This image was taken at a distance · the lesion involves the back of the hand and arm · the patient is a female aged 30–39: 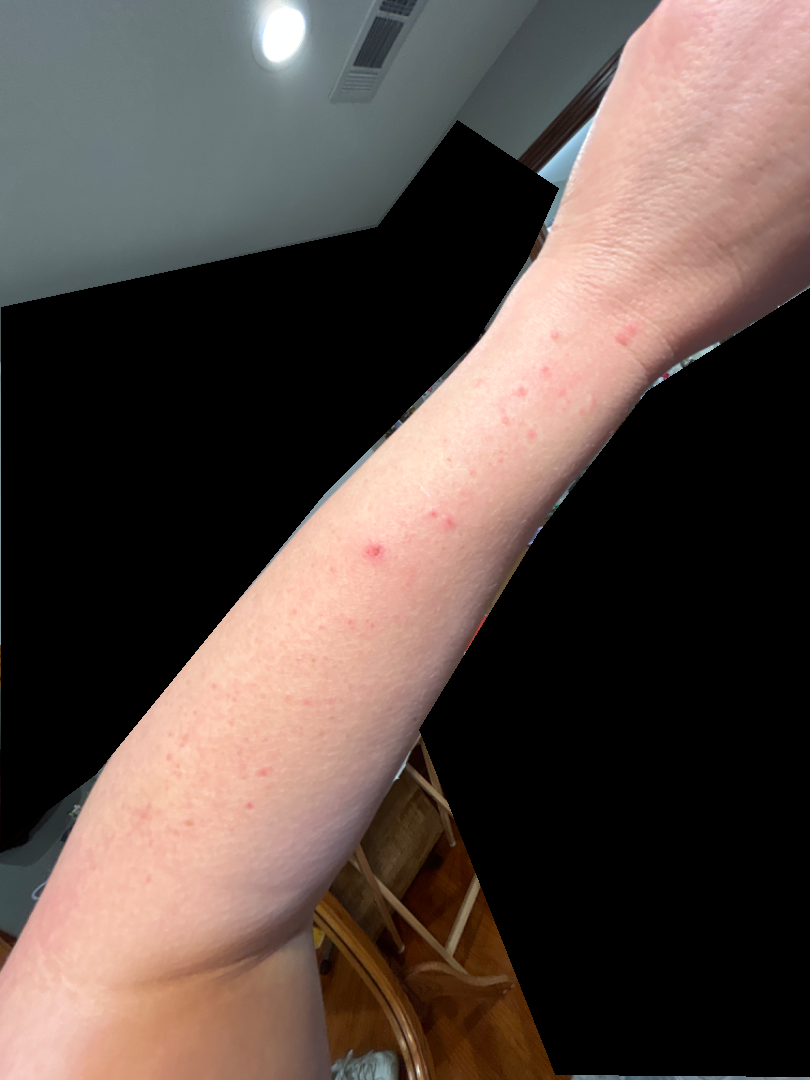On photographic review: Allergic Contact Dermatitis (36%); Urticaria (20%); Insect Bite (20%); Viral Exanthem (14%); Folliculitis (9%).